A dermoscopic image of a skin lesion.
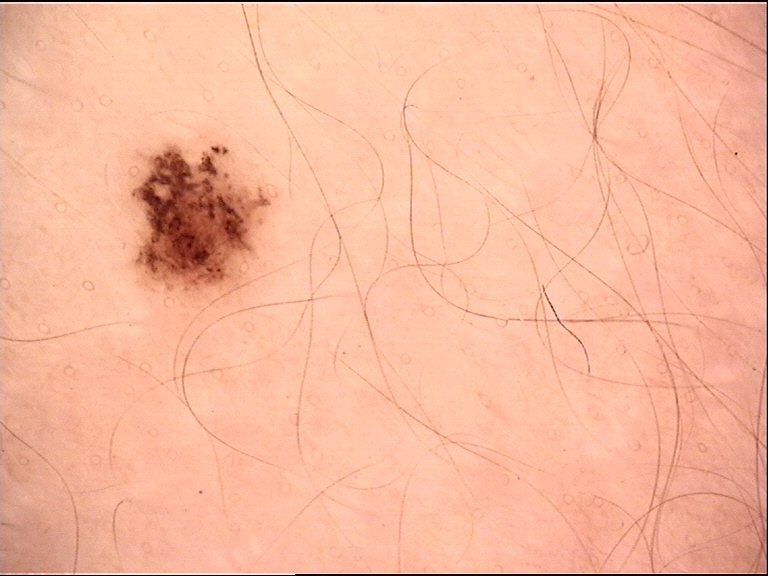diagnosis:
  name: dysplastic junctional nevus
  code: jd
  malignancy: benign
  super_class: melanocytic
  confirmation: expert consensus